The contributor reports the lesion is raised or bumpy. Skin tone: lay reviewers estimated 2 on the MST. The photograph was taken at an angle. The leg is involved. Reported duration is less than one week:
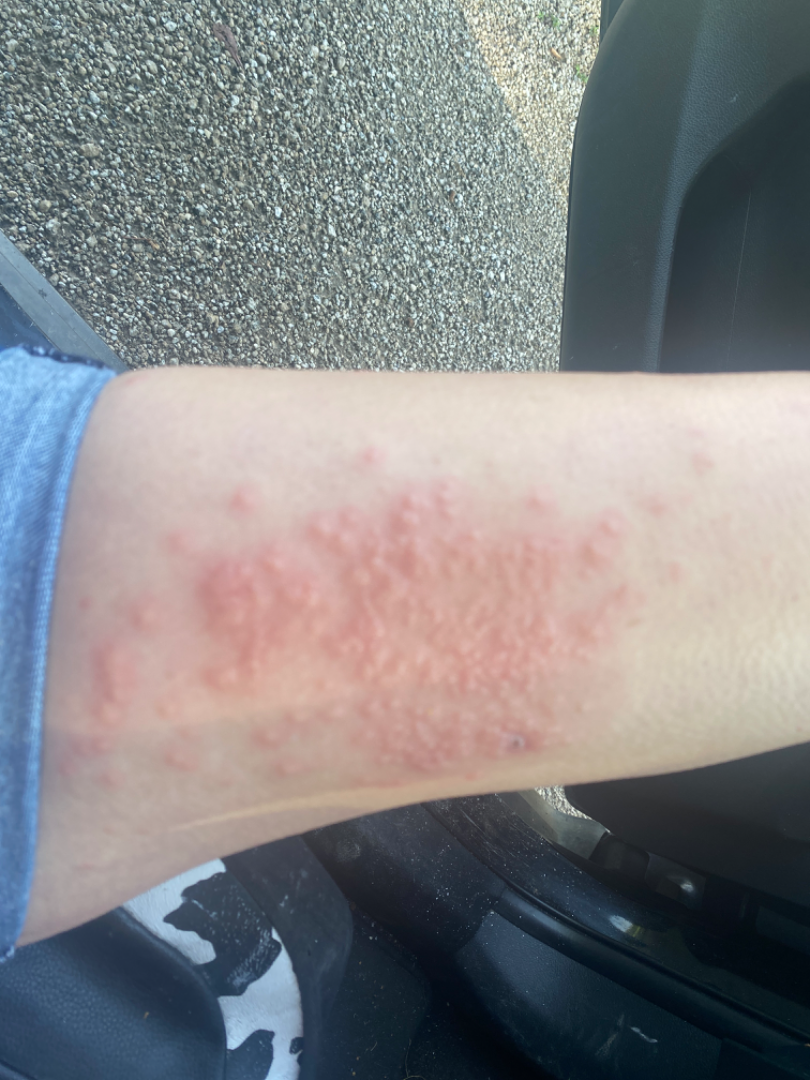| key | value |
|---|---|
| assessment | indeterminate |